Close-up view:
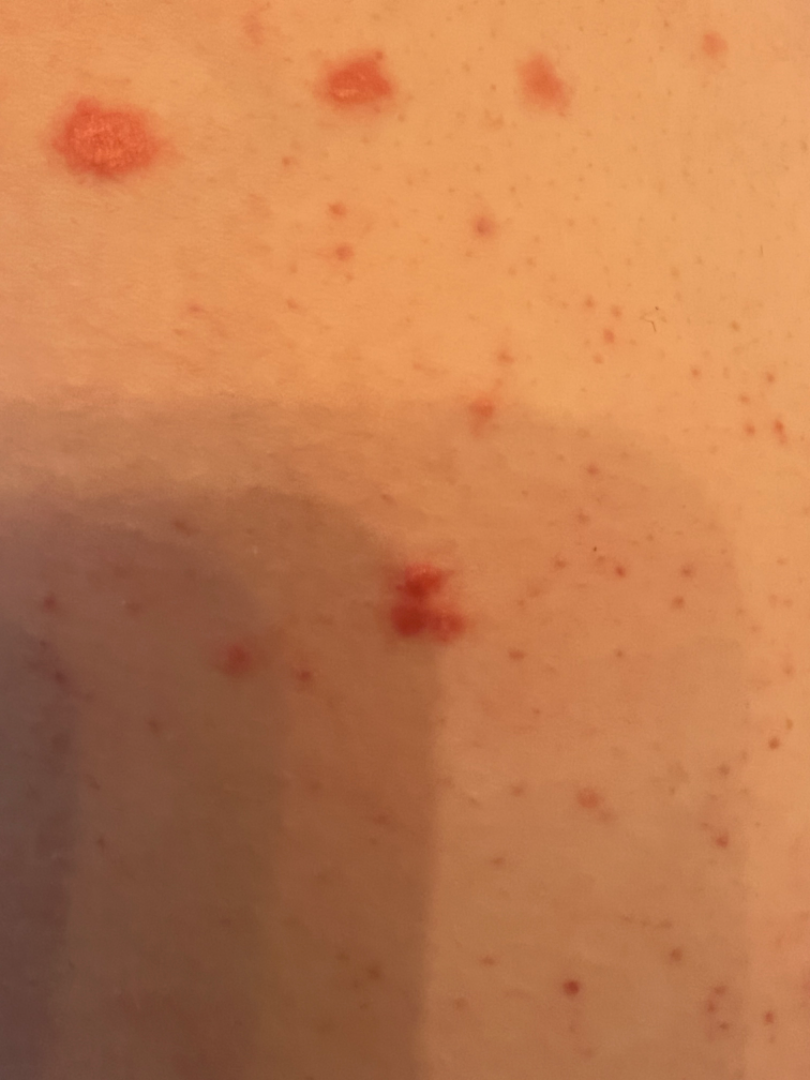{
  "assessment": "not assessable"
}